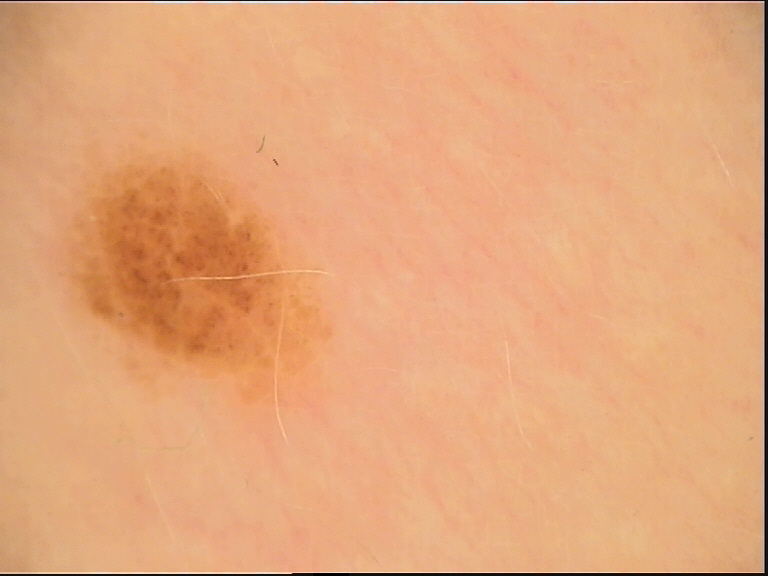– diagnostic label — dysplastic compound nevus (expert consensus)